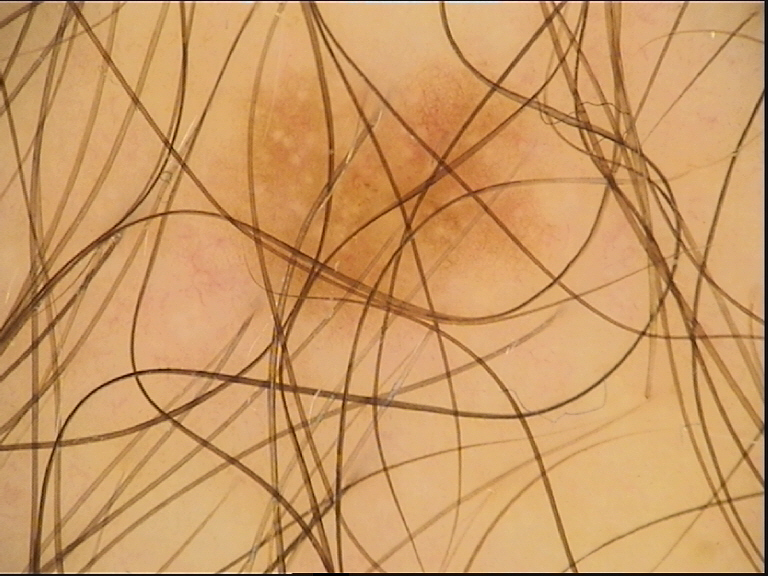The diagnostic label was a dysplastic junctional nevus.